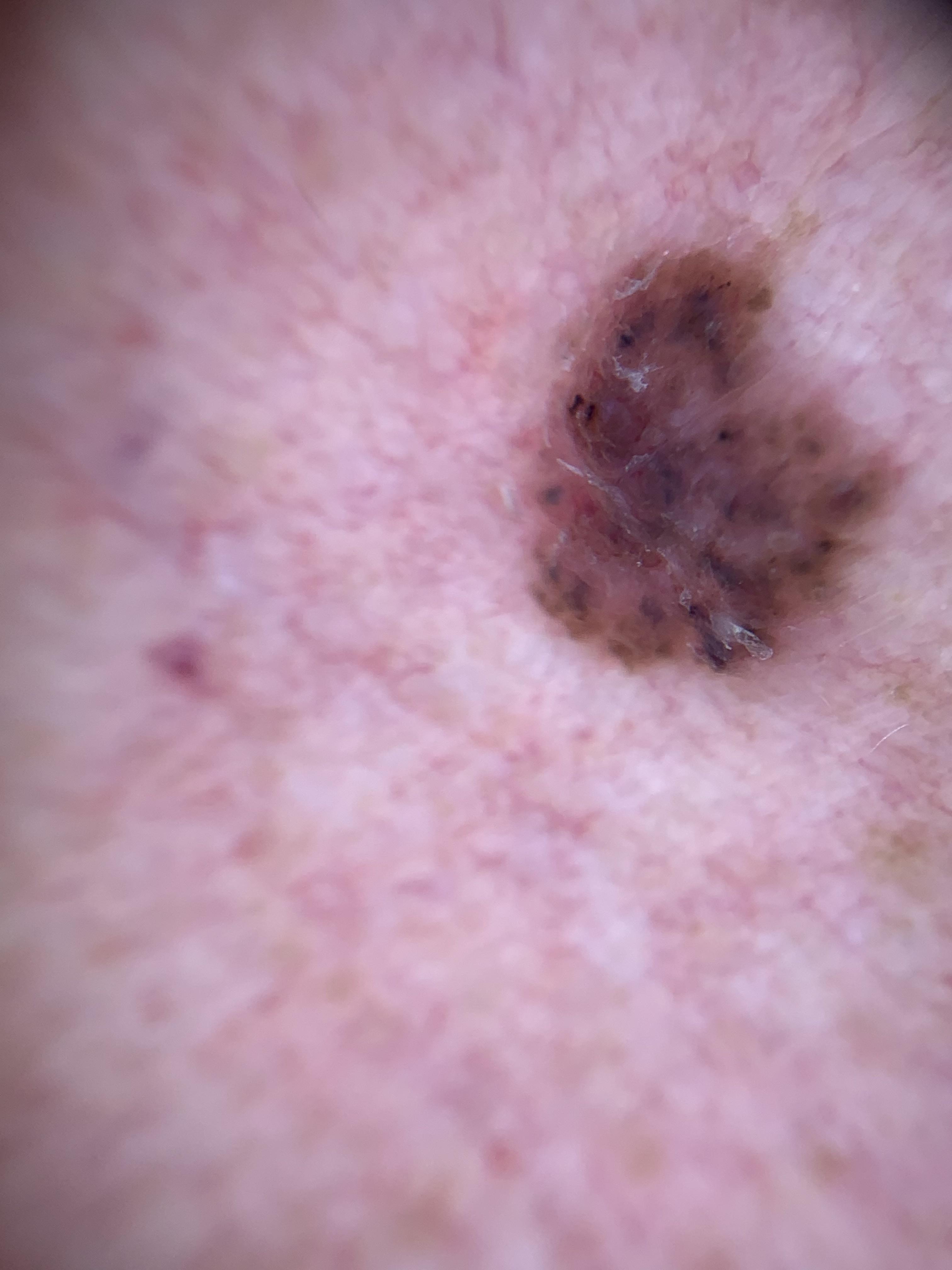<lesion>
<skin_type>II</skin_type>
<image>dermoscopy</image>
<patient>
<age_approx>55</age_approx>
<sex>female</sex>
</patient>
<lesion_location>
<region>the trunk</region>
<detail>the anterior trunk</detail>
</lesion_location>
<diagnosis>
<name>Basal cell carcinoma</name>
<malignancy>malignant</malignancy>
<confirmation>histopathology</confirmation>
<lineage>adnexal</lineage>
</diagnosis>
</lesion>